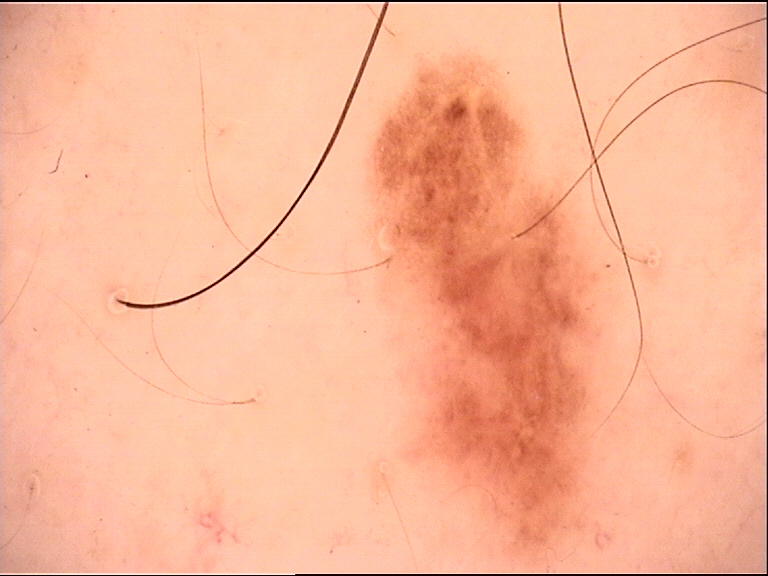Case:
– assessment · dysplastic junctional nevus (expert consensus)